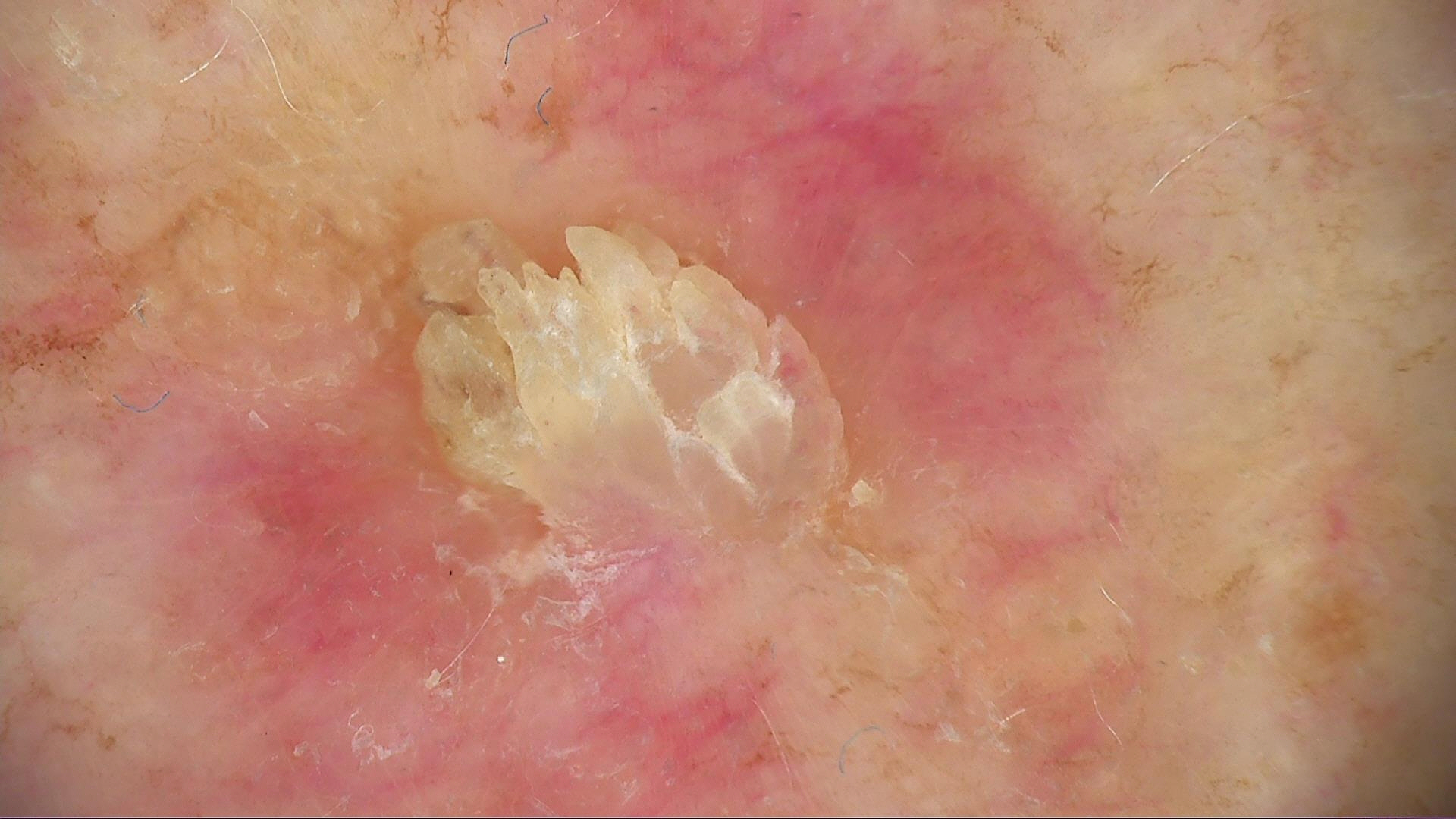imaging: dermoscopy, lesion type: keratinocytic, diagnostic label: cutaneous horn (biopsy-proven).